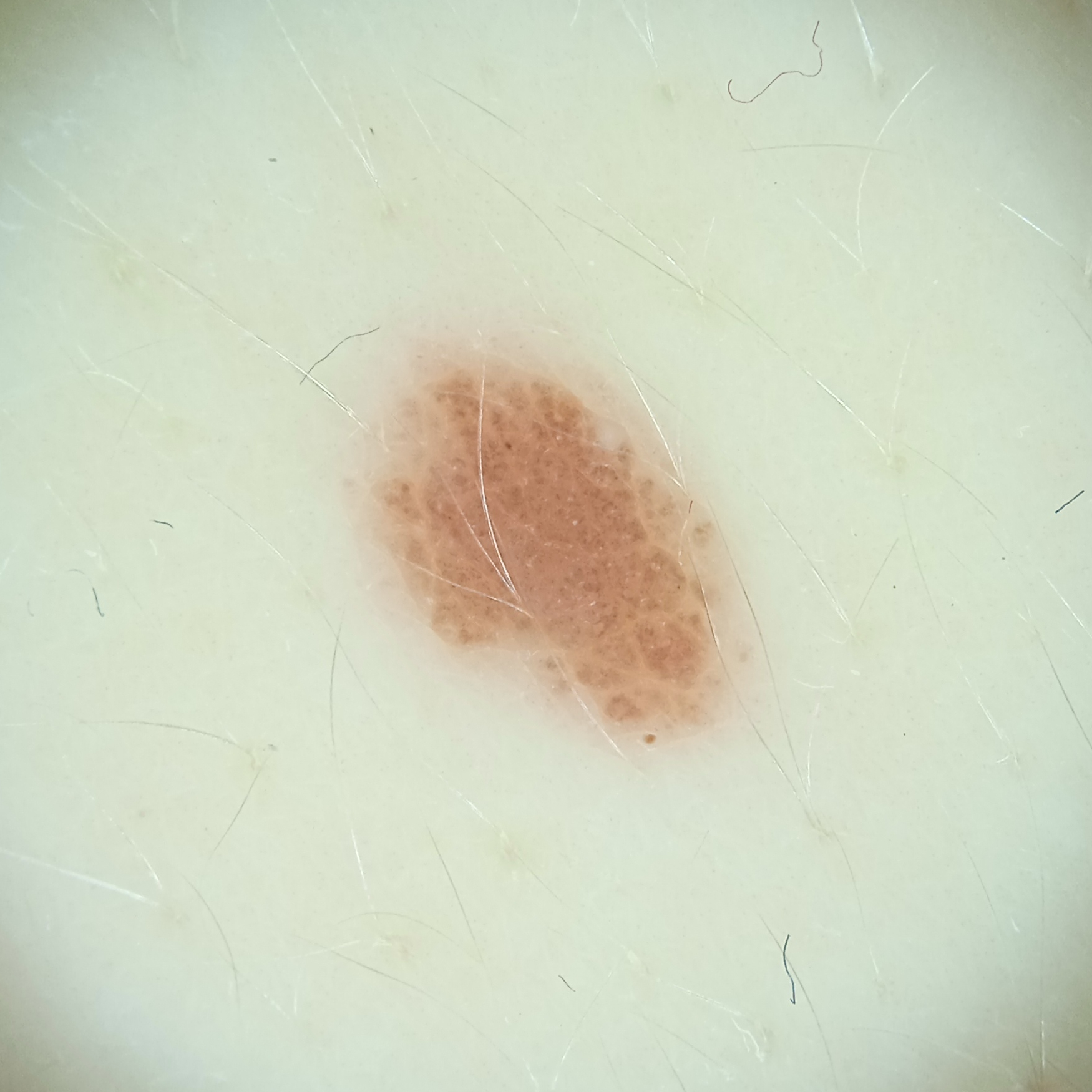subject: female, aged 20; body site: the torso; diameter: 5.1 mm; diagnosis: melanocytic nevus (dermatologist consensus).